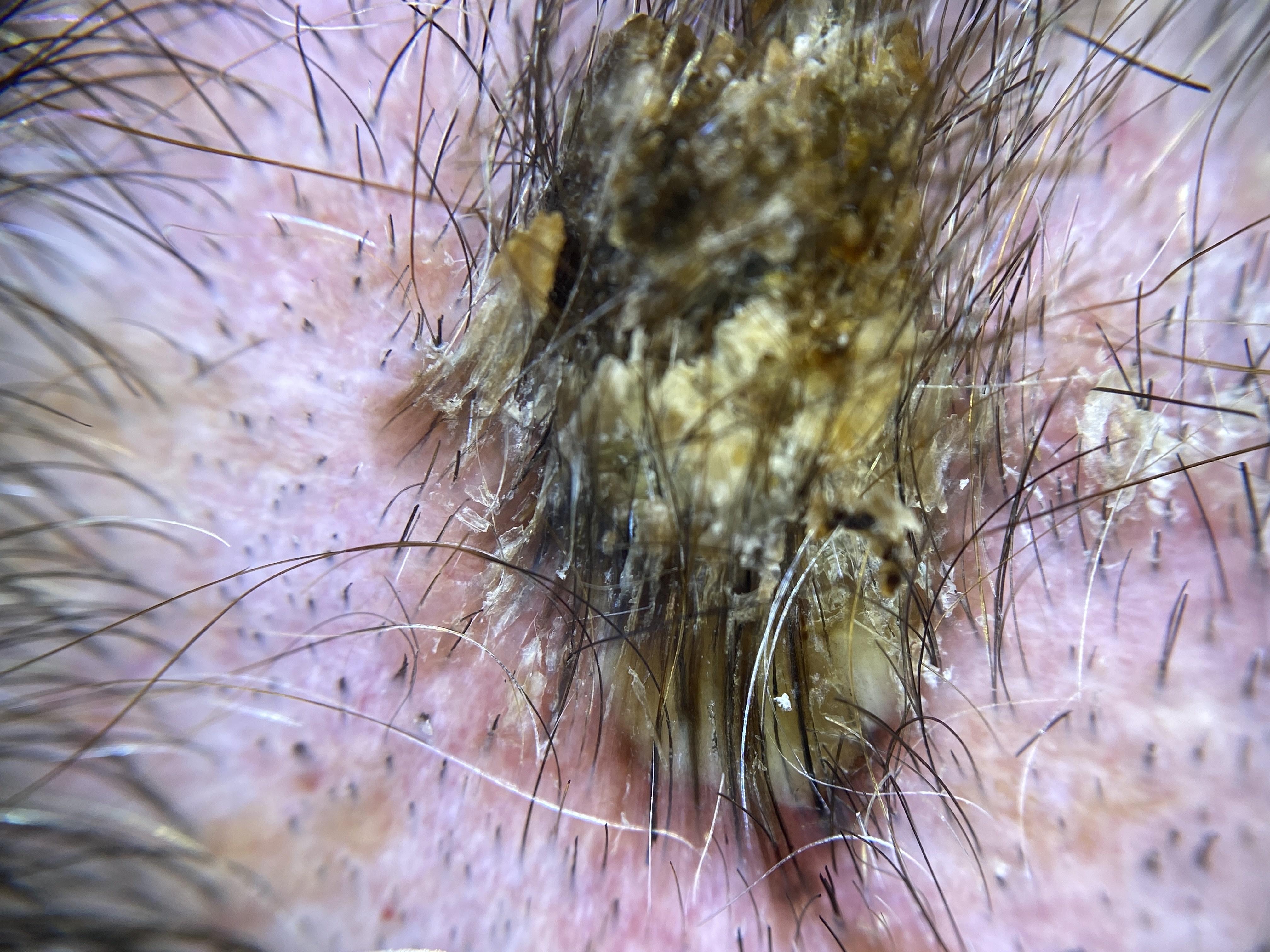The lesion is located on the head or neck.
The biopsy diagnosis was a tumor of follicular differentiation — a basal cell carcinoma.